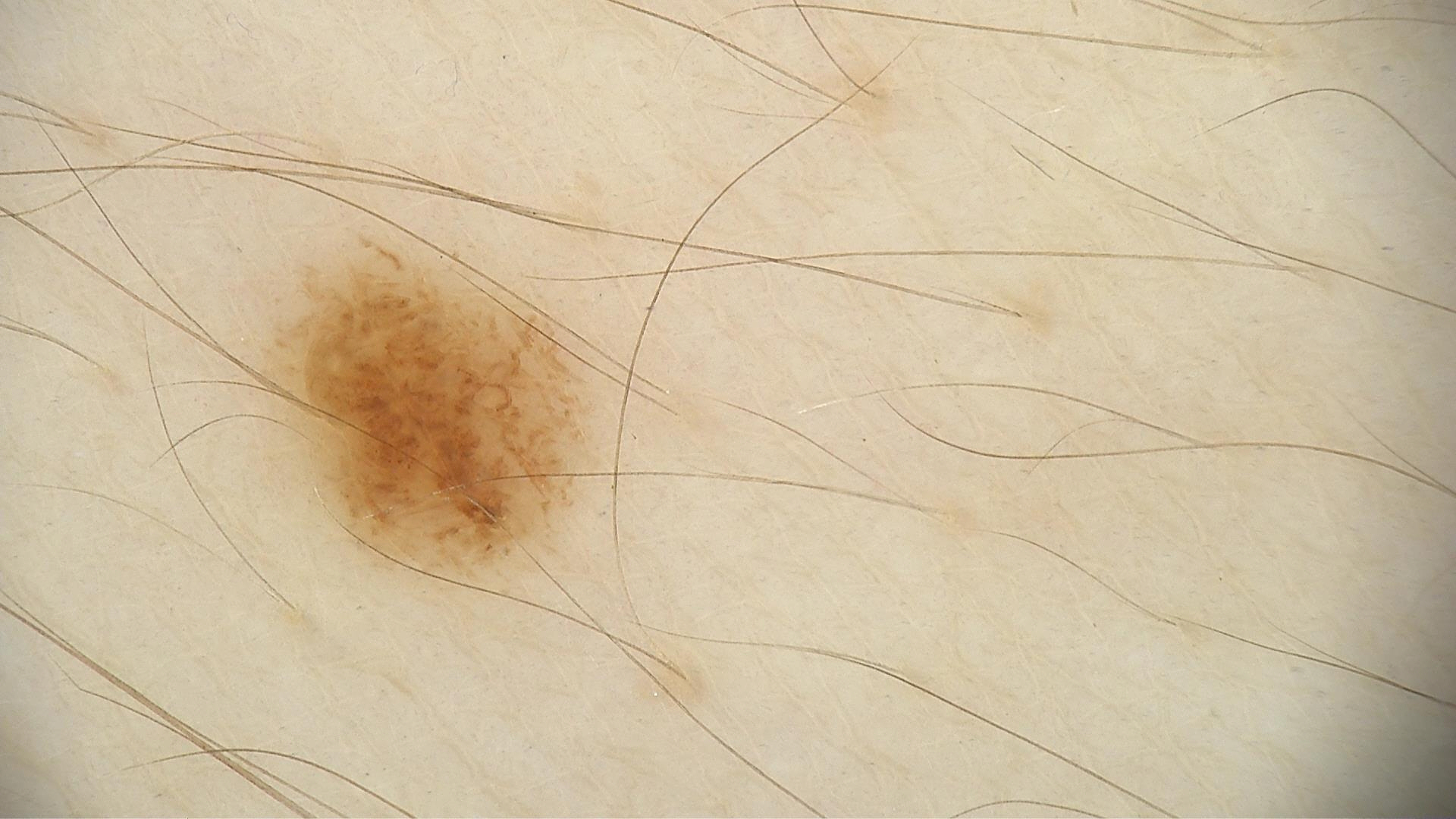Diagnosed as a dysplastic junctional nevus.